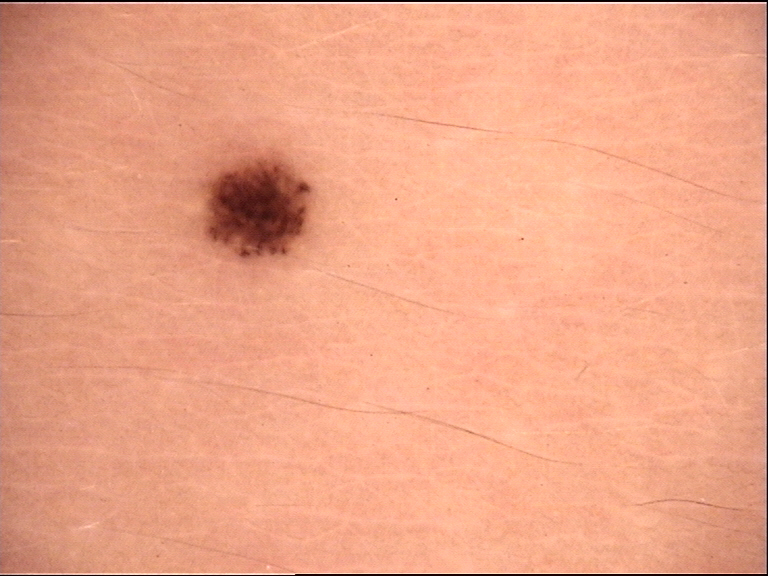Conclusion: Consistent with a dysplastic junctional nevus.